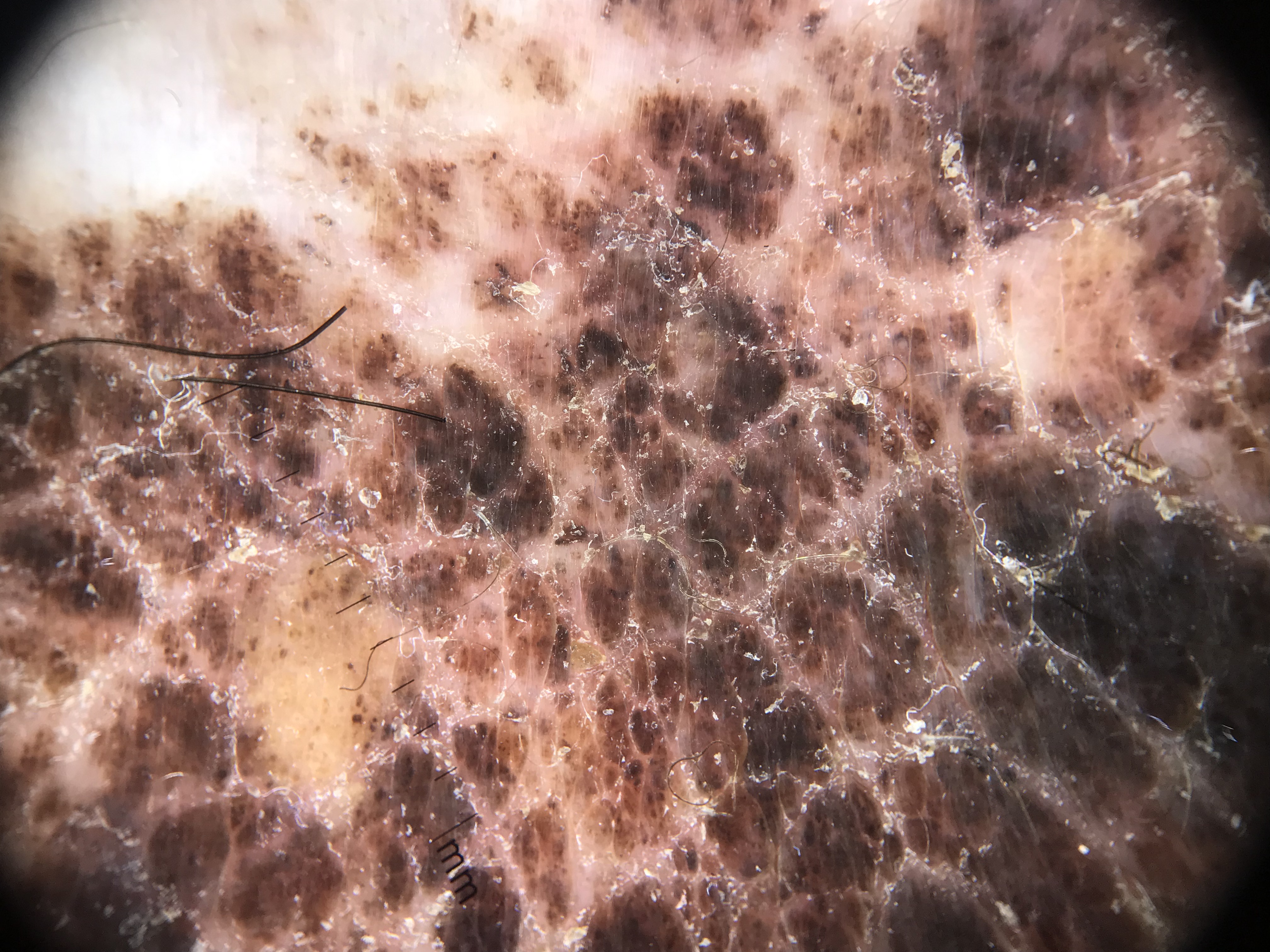The diagnostic label was a congenital compound nevus.